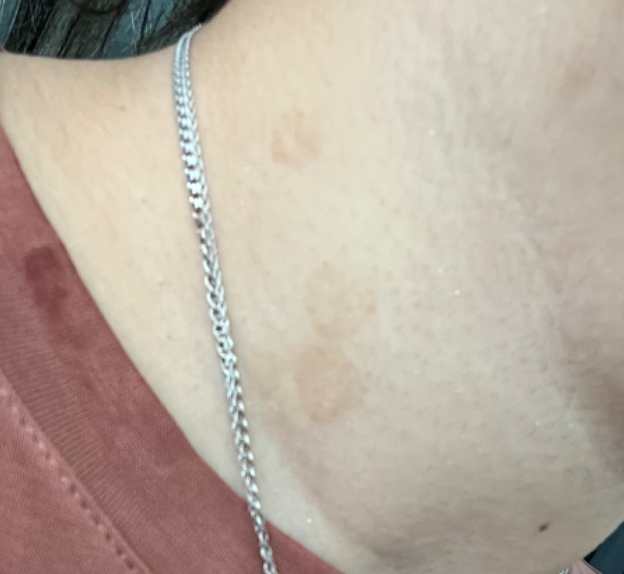The condition has been present for about one day.
The patient reported no relevant symptoms from the lesion.
This is a close-up image.
The contributor reports the lesion is raised or bumpy.
The head or neck is involved.
The subject is 18–29, female.
No relevant systemic symptoms.
Self-categorized by the patient as a rash.
The reviewing dermatologists' impression was: favoring Tinea Versicolor; lower on the differential is Seborrheic Dermatitis; less likely is Eczema; a remote consideration is Tinea.